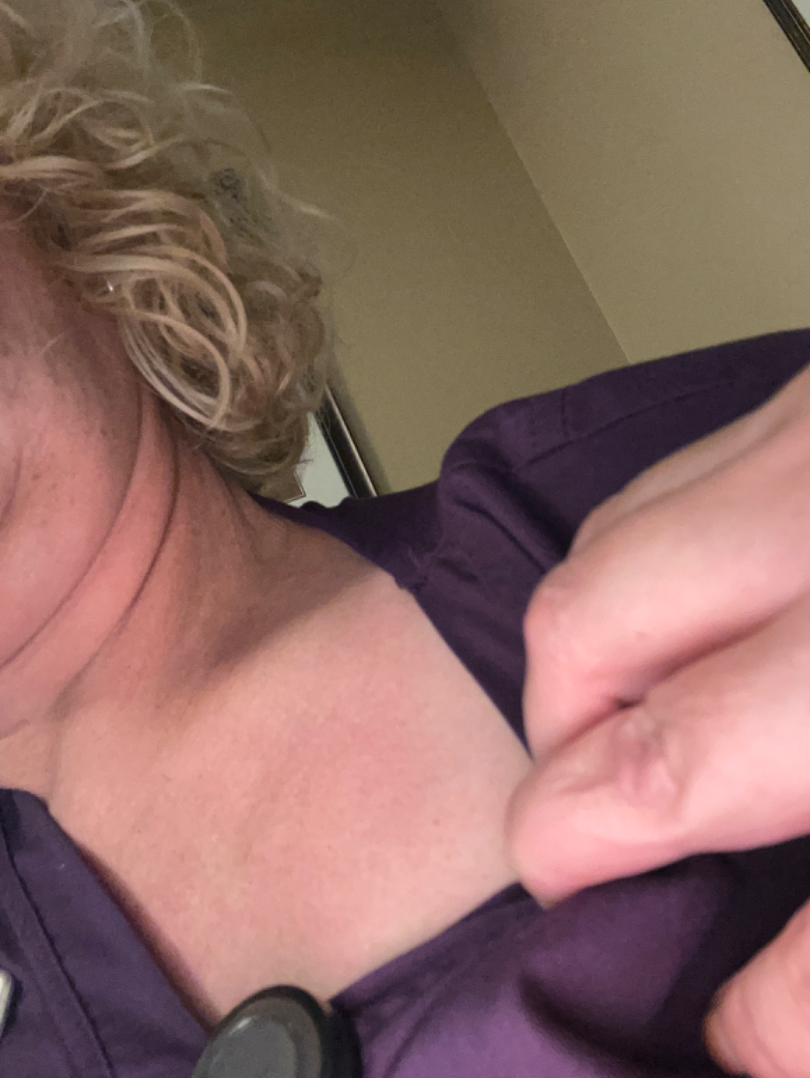Review:
The reviewing dermatologist did not identify a discernible skin condition.